This is a close-up image · the head or neck, leg and arm are involved.
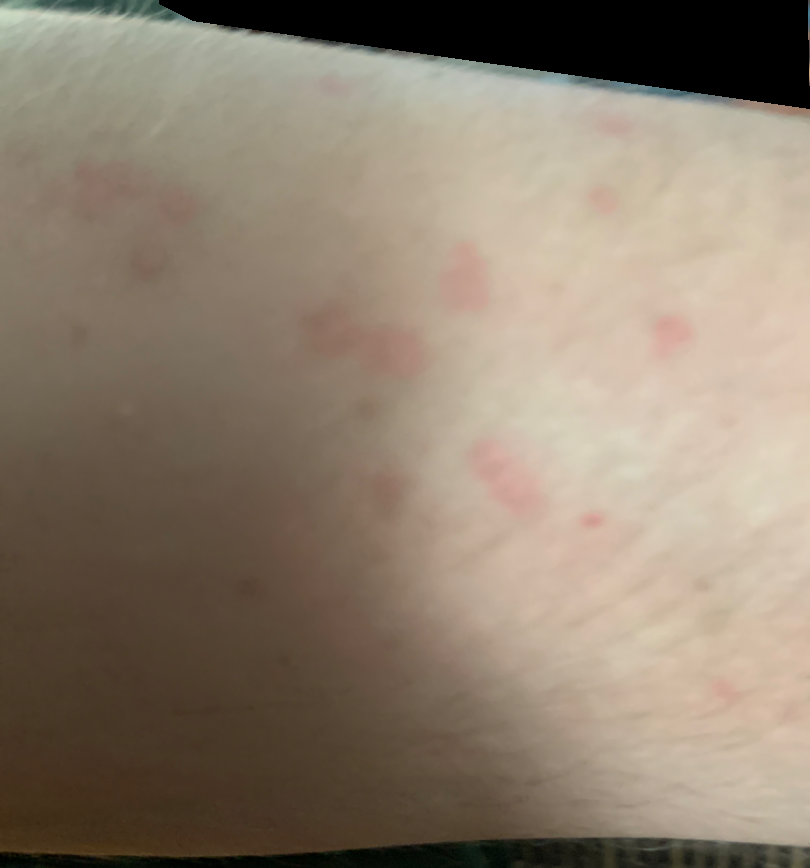The reviewing dermatologist was unable to assign a differential diagnosis from the image.